A dermoscopy image of a single skin lesion: 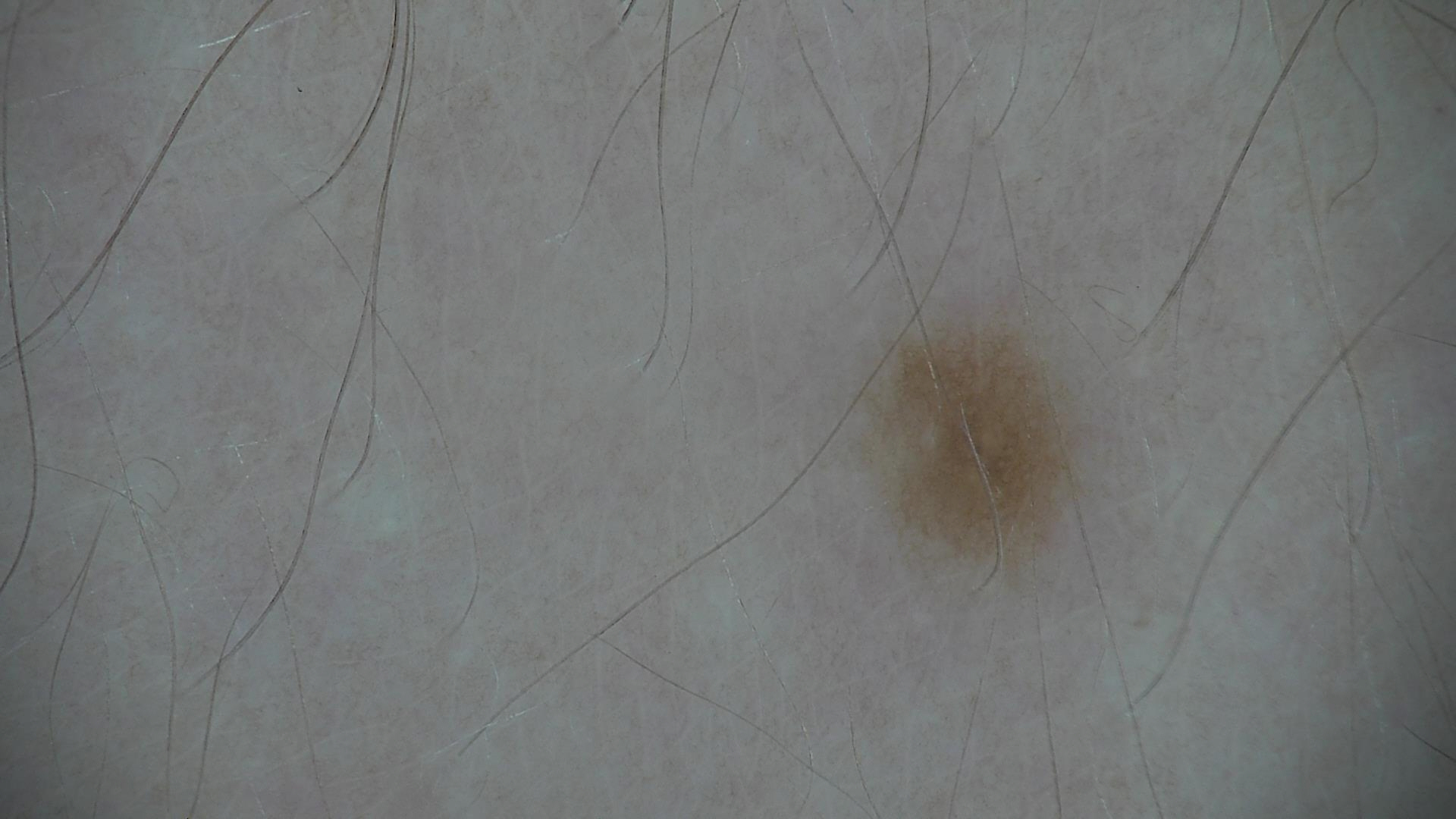diagnosis:
  name: dysplastic junctional nevus
  code: jd
  malignancy: benign
  super_class: melanocytic
  confirmation: expert consensus